The photo was captured at a distance.
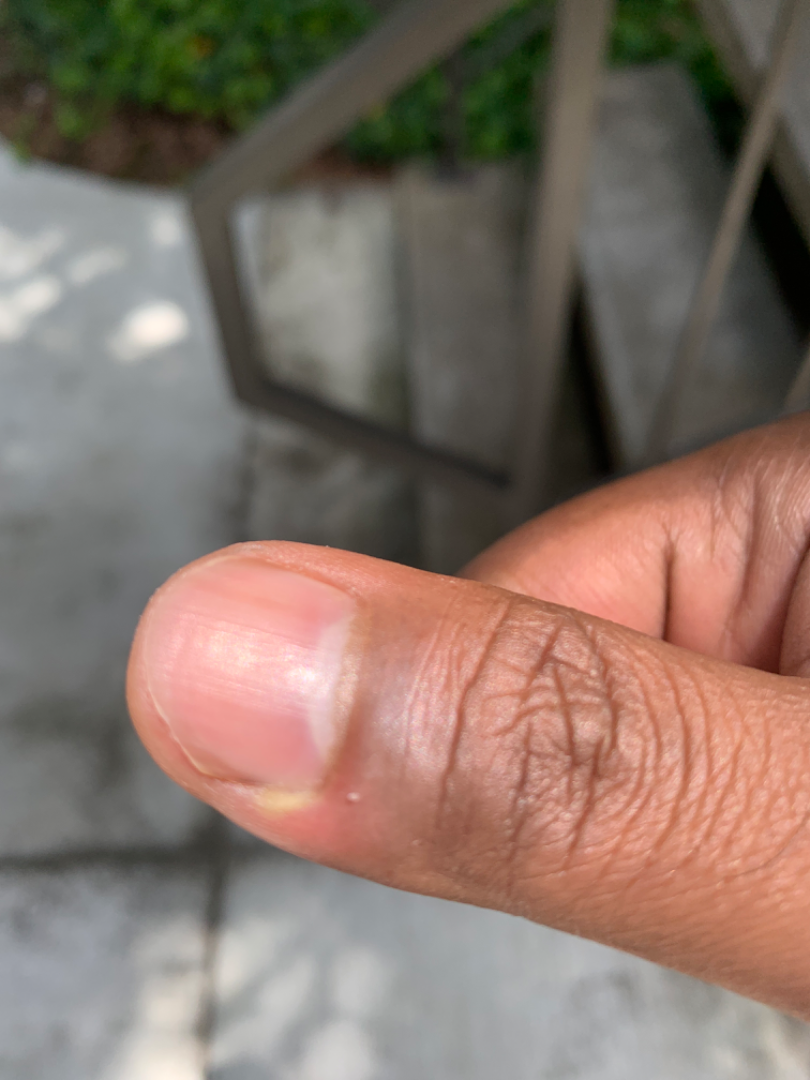Q: Patient's own categorization?
A: a rash
Q: What is the dermatologist's impression?
A: a single dermatologist reviewed the case: most consistent with Paronychia; the differential also includes Herpes Simplex; possibly Eczema